A female subject 75 years old. A skin lesion imaged with a dermatoscope. The patient reports a personal history of cancer and a personal history of skin cancer. The patient says their skin tans without first burning. The patient describes having a moderate number of moles. Imaged for a research study, with no referral diagnosis recorded:
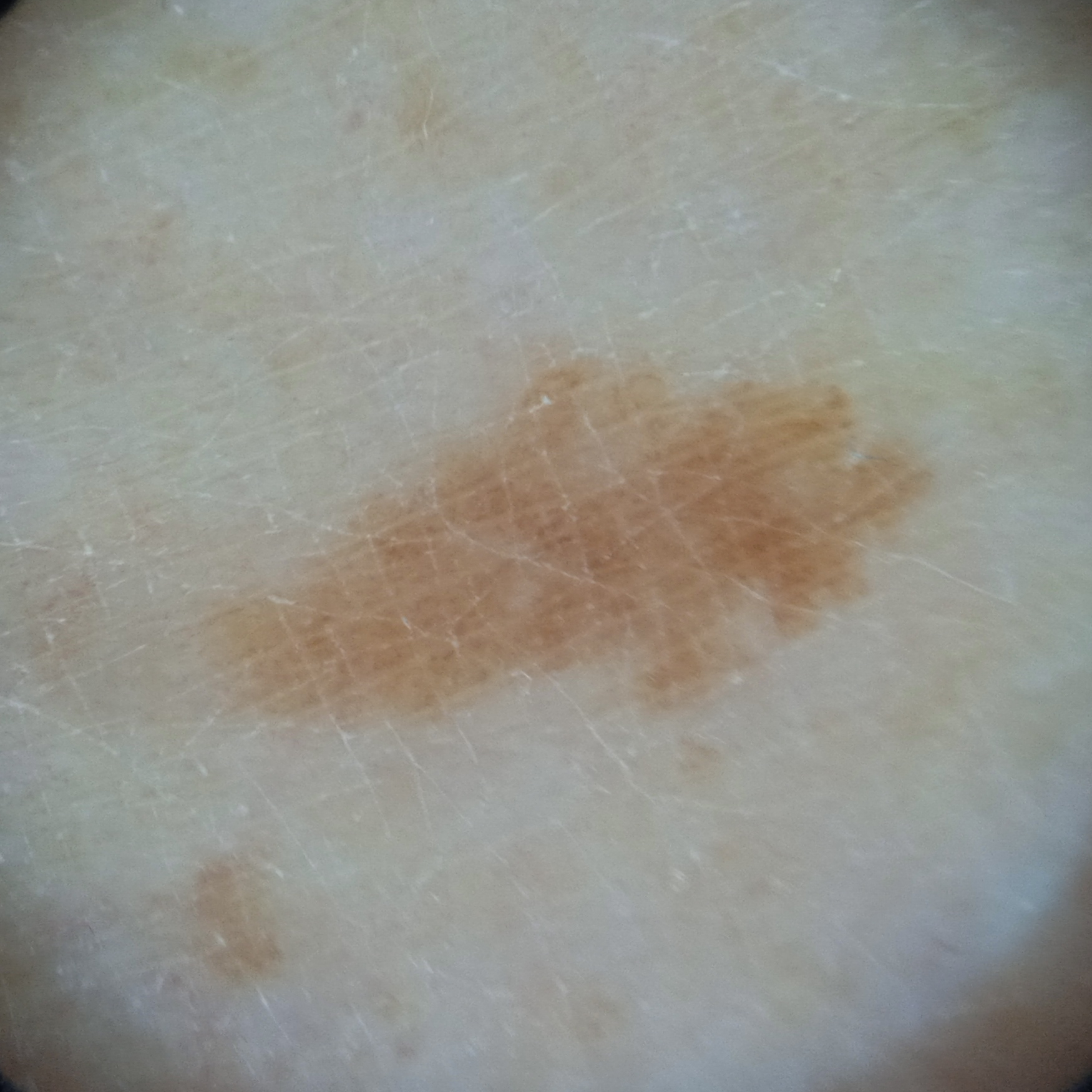{
  "lesion_location": "a leg",
  "lesion_size": {
    "diameter_mm": 8.2
  },
  "diagnosis": {
    "name": "melanocytic nevus",
    "malignancy": "benign"
  }
}